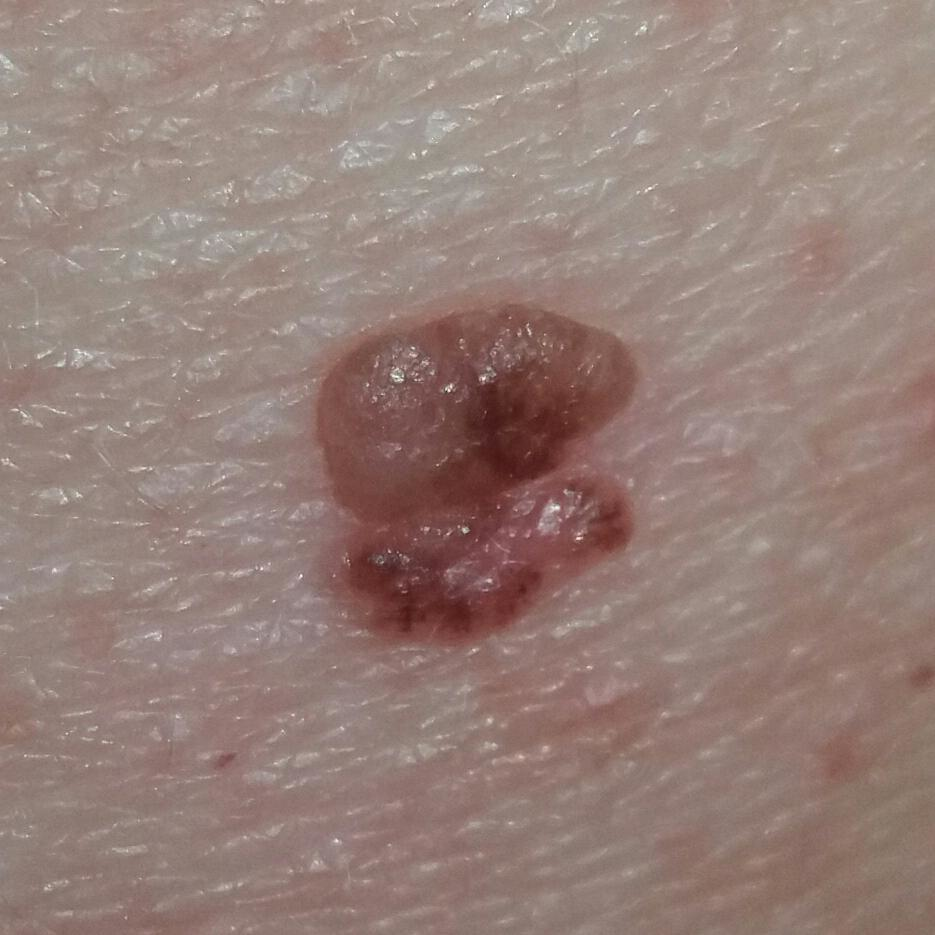| feature | finding |
|---|---|
| skin type | II |
| subject | female, in their mid-50s |
| site | the back |
| diameter | 6 × 5 mm |
| patient-reported symptoms | elevation, growth |
| diagnosis | basal cell carcinoma (biopsy-proven) |